A skin lesion imaged with a dermatoscope.
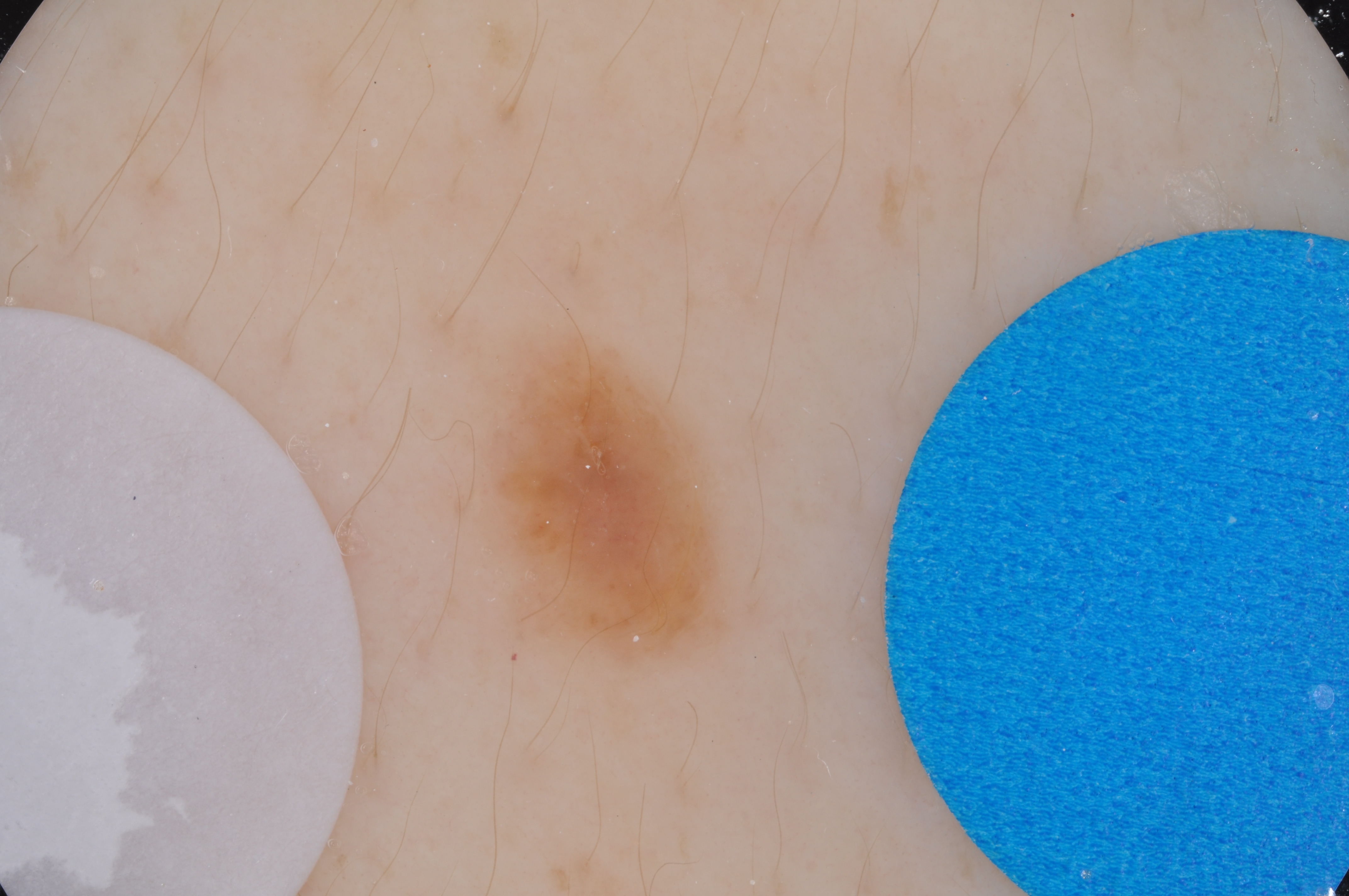Image and clinical context: Dermoscopic assessment notes no negative network, milia-like cysts, pigment network, globules, or streaks. A small lesion occupying a minor part of the field. With coordinates (x1, y1, x2, y2), the lesion is located at bbox=[485, 316, 729, 672]. Conclusion: The diagnostic assessment was a melanocytic nevus.